Skin tone: Fitzpatrick skin type IV; the patient is 50–59, male; reported duration is one to four weeks; an image taken at an angle; the patient described the issue as skin that appeared healthy to them; symptoms reported: bothersome appearance, itching and enlargement; located on the palm, leg, back of the hand, head or neck and arm; the contributor notes the lesion is raised or bumpy.
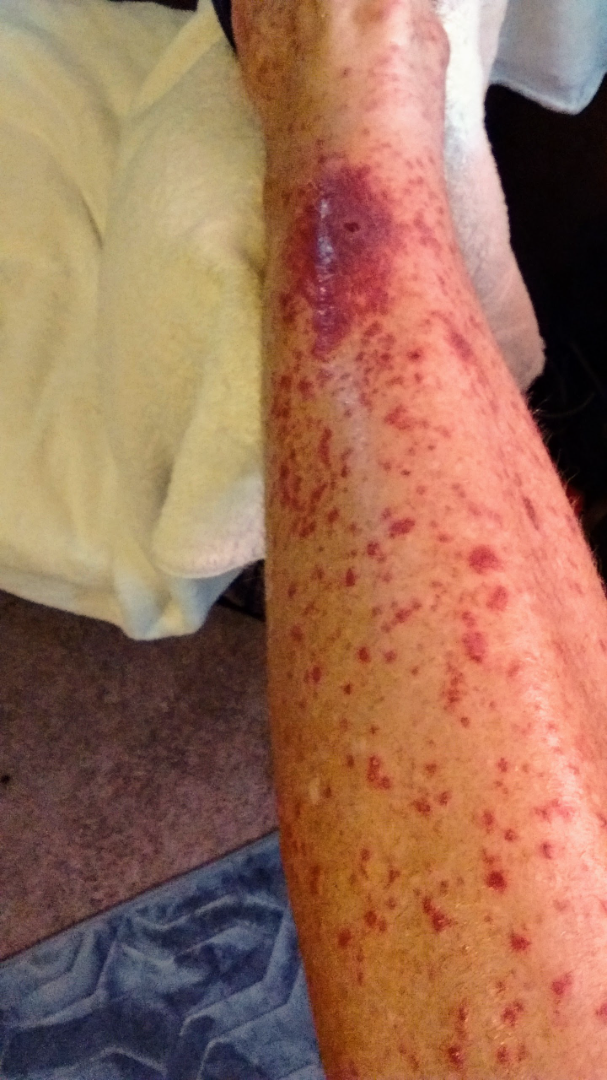Q: What is the differential diagnosis?
A: the favored diagnosis is Leukocytoclastic Vasculitis